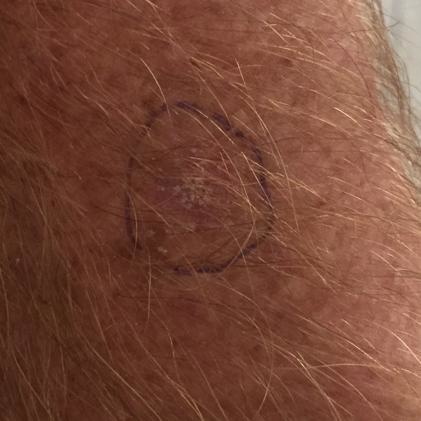Notes:
- patient: male, in their 50s
- image type: clinical photo
- patient-reported symptoms: itching / no bleeding
- diagnostic label: actinic keratosis (clinical consensus)